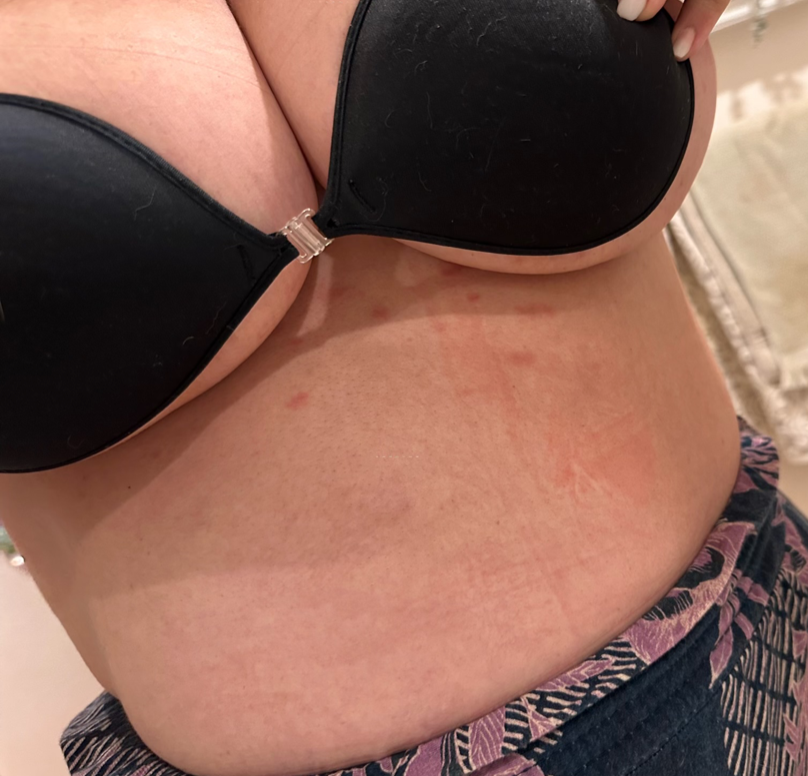On photographic review by a dermatologist, the primary impression is Pityriasis rosea; with consideration of Lichen planus/lichenoid eruption; less probable is Syphilis.